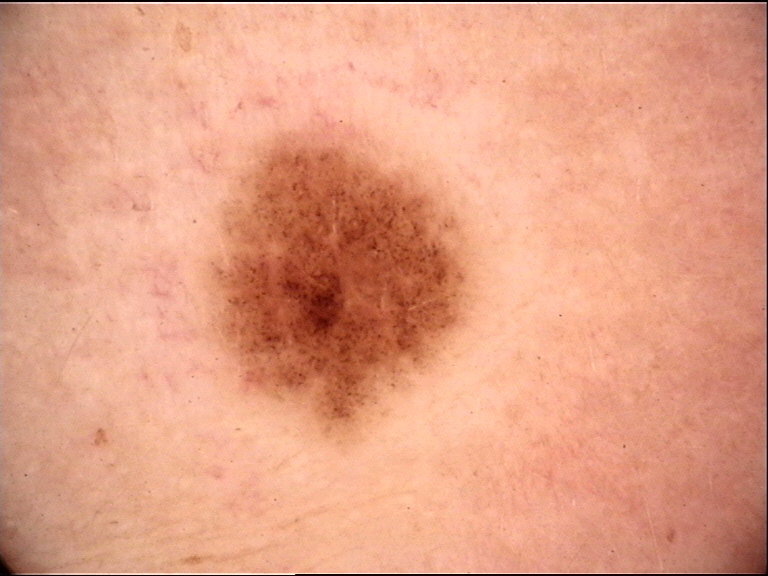Consistent with a dysplastic junctional nevus.